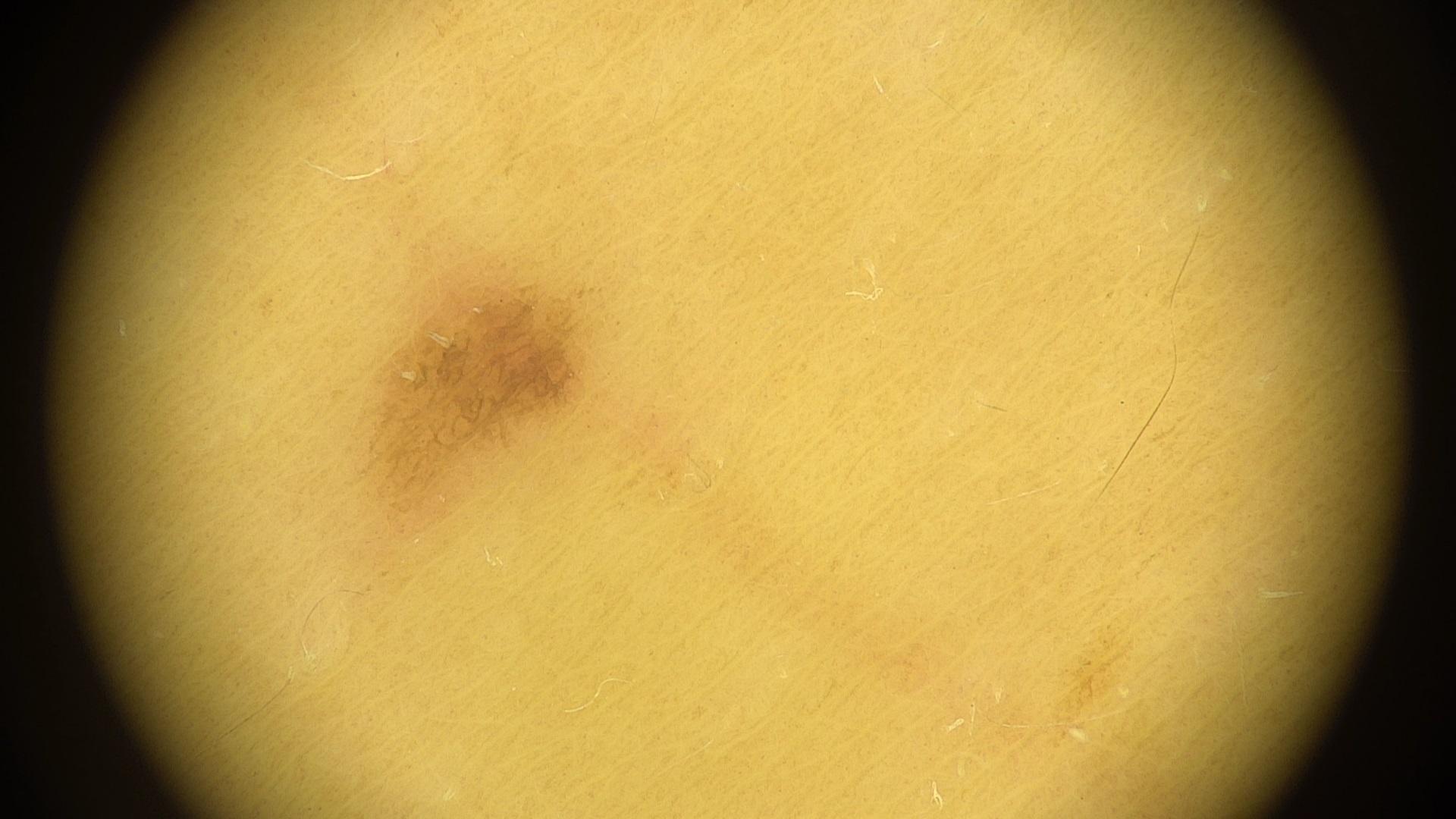A female patient aged 33 to 37. Recorded as Fitzpatrick phototype II. The lesion is located on a lower extremity. The clinical impression was a benign lesion — a nevus.